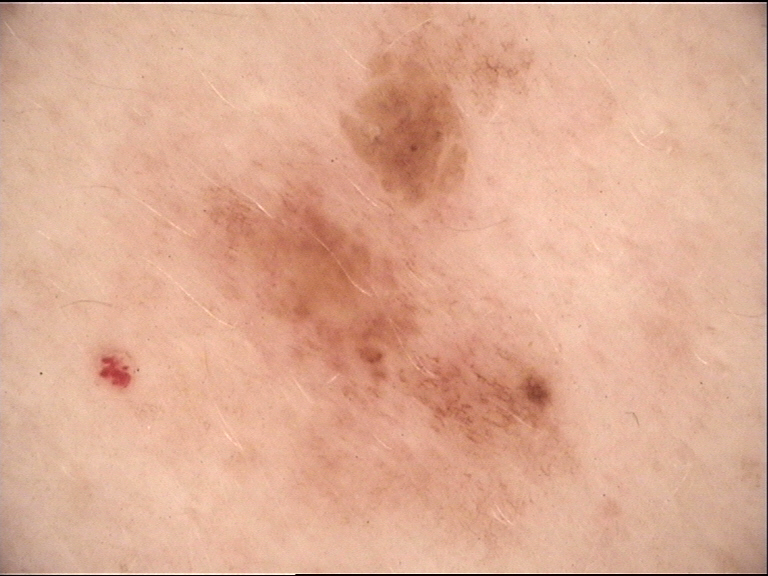Findings: A dermoscopic close-up of a skin lesion. Impression: Classified as a benign lesion — a dysplastic junctional nevus.